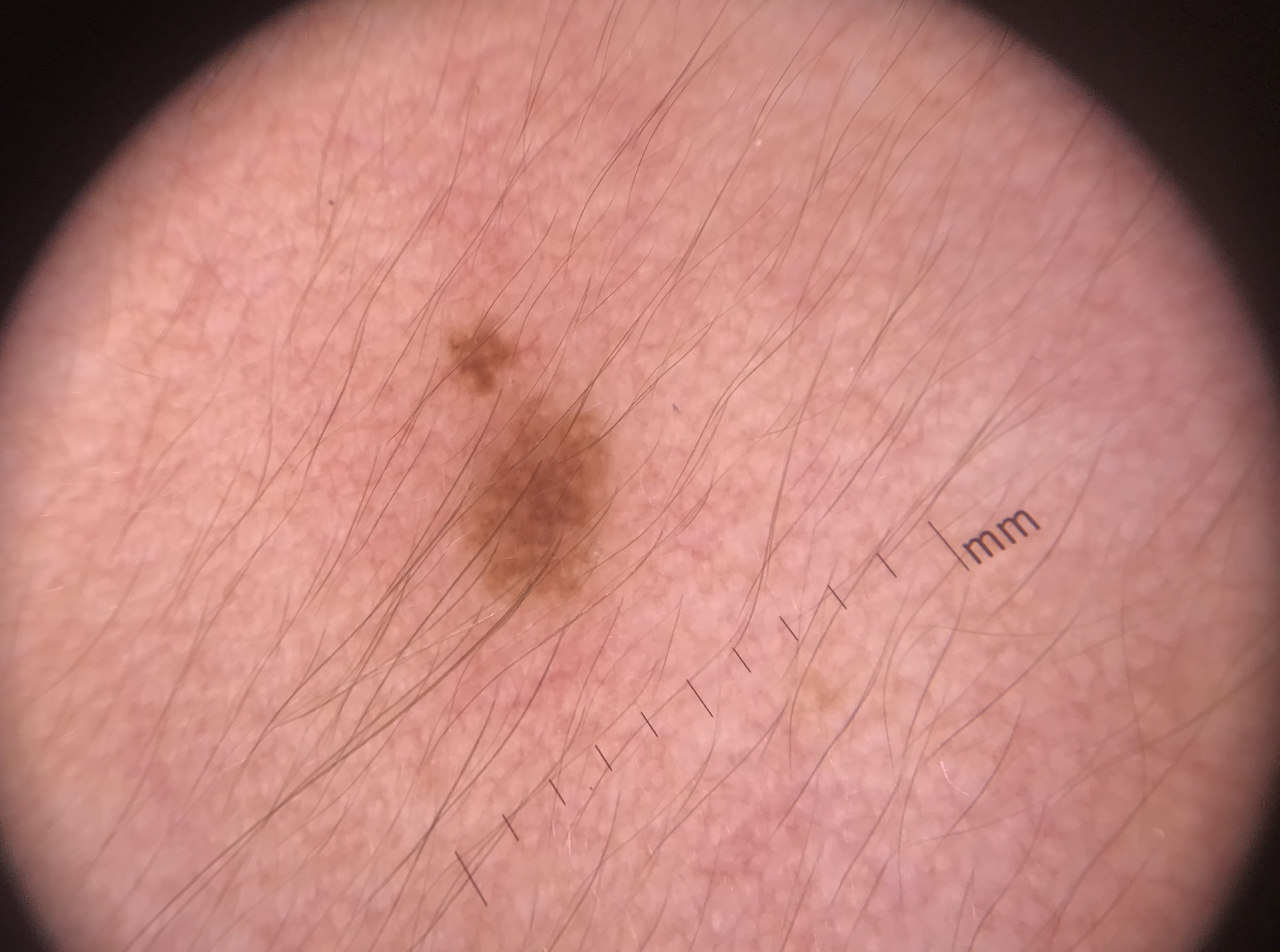image type: dermoscopy | diagnostic label: junctional nevus (expert consensus).